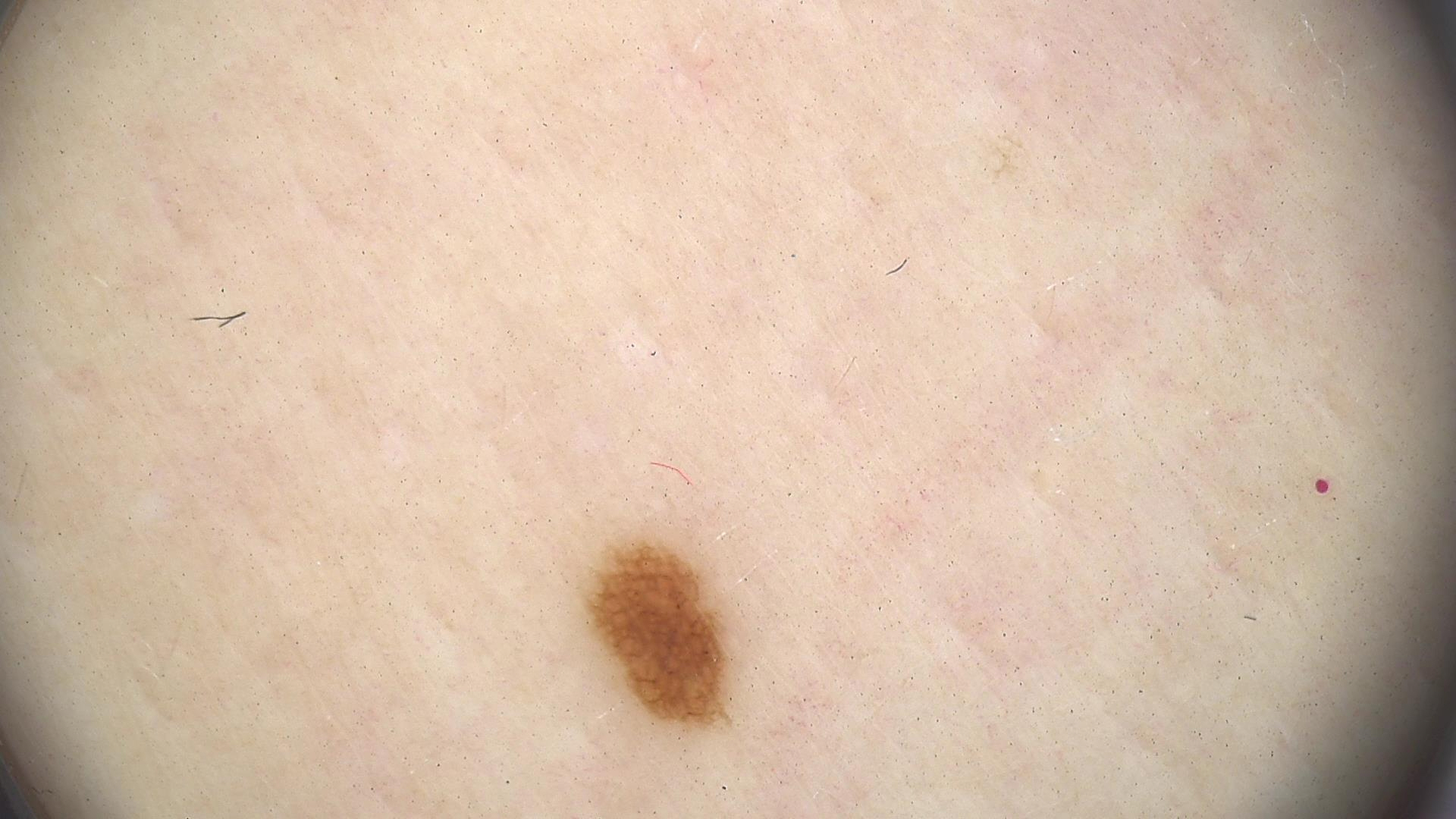Classified as a banal lesion — a junctional nevus.